Dermoscopy of a skin lesion.
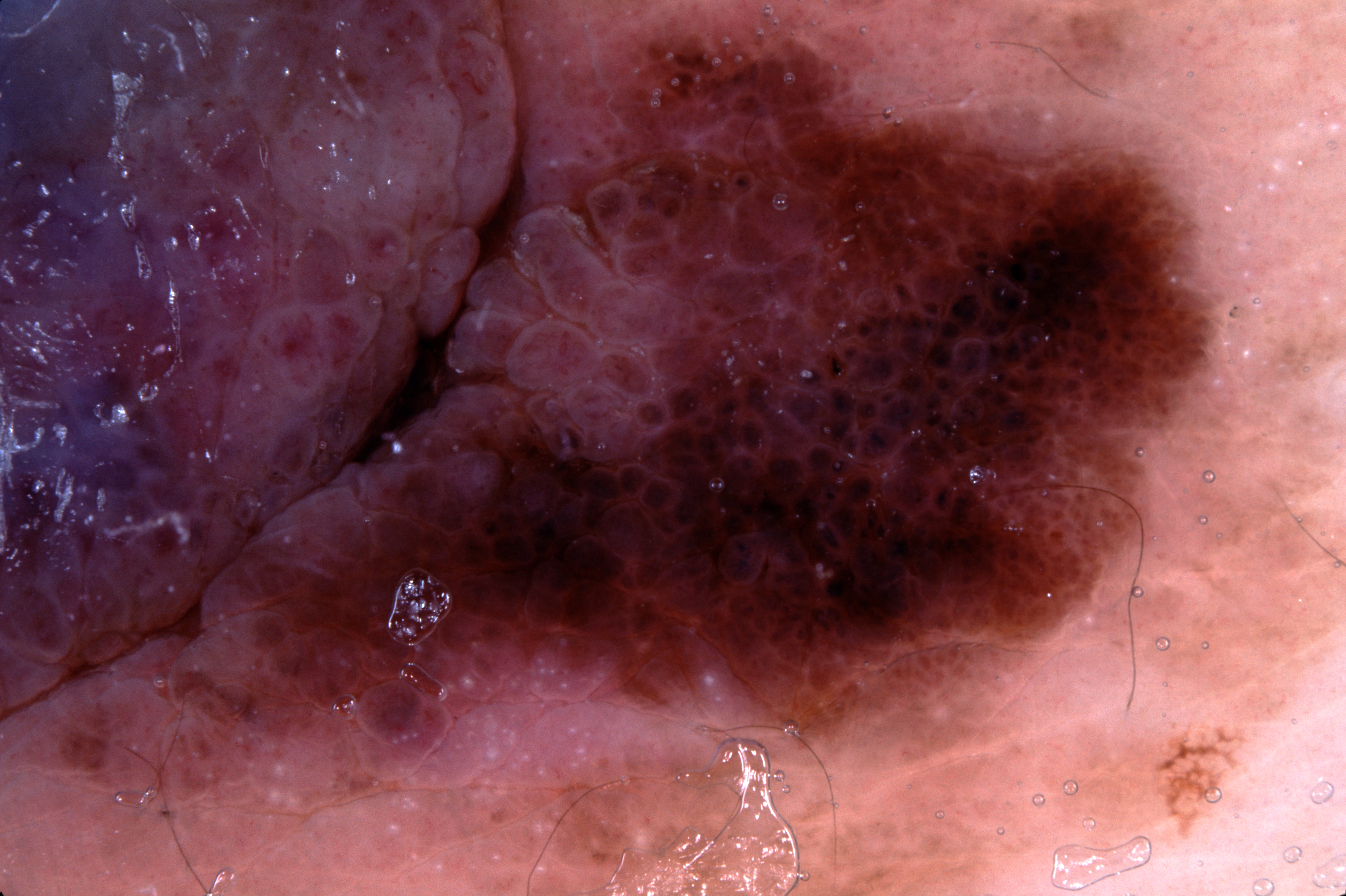Findings: As (left, top, right, bottom), lesion location: 0, 0, 1209, 826. The dermoscopic pattern shows negative network and milia-like cysts. Pathology: The biopsy diagnosis was a melanoma.